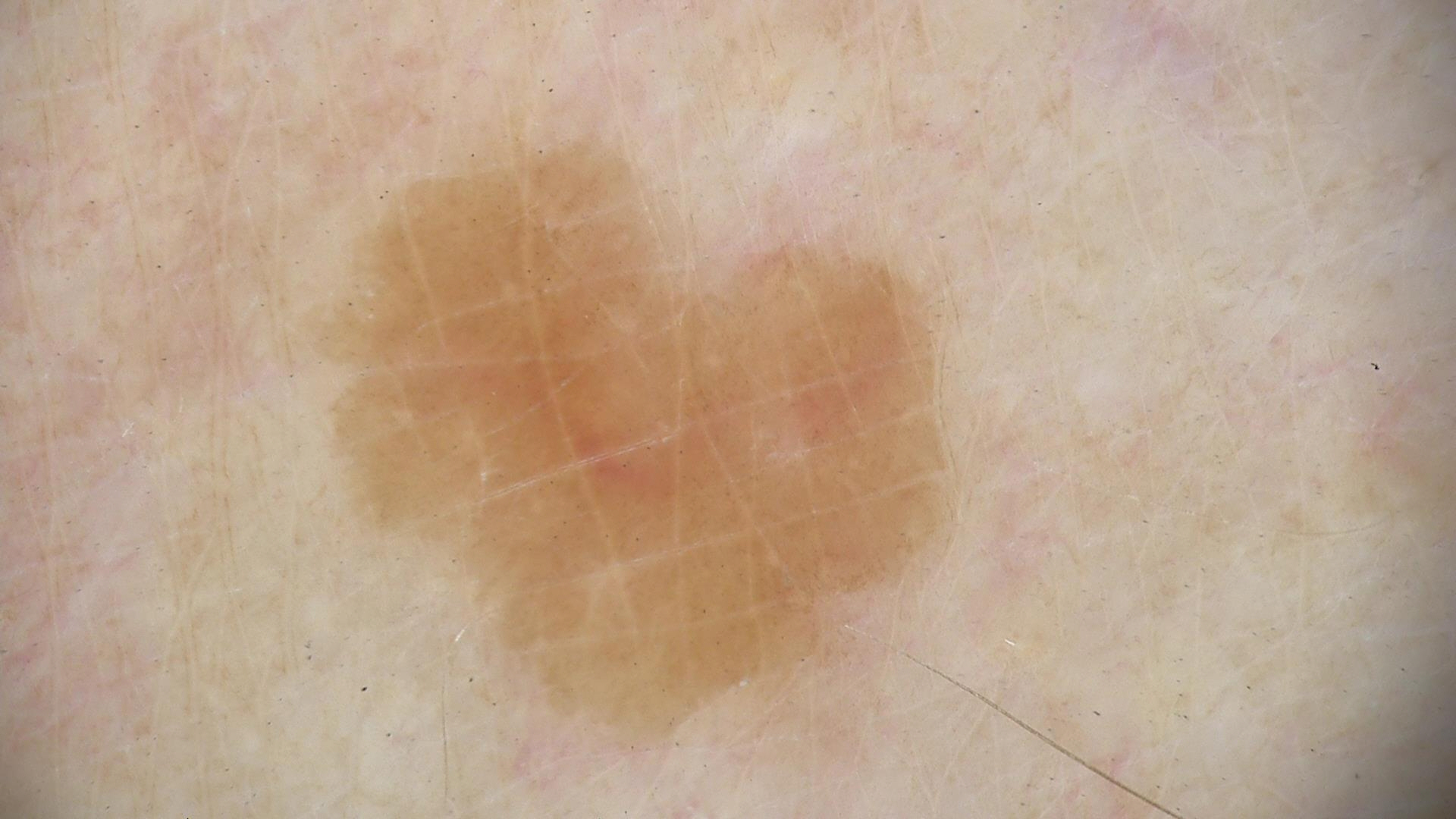Findings:
A dermoscopic photograph of a skin lesion. The morphology is that of a keratinocytic lesion.
Impression:
The diagnosis was a benign lesion — a seborrheic keratosis.